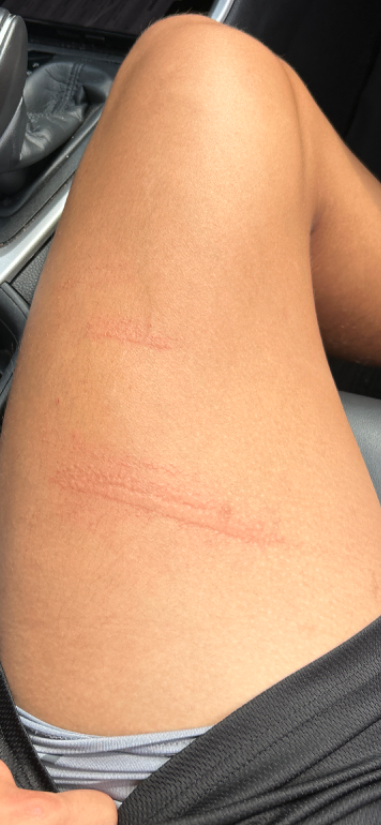Clinical context:
The patient indicates the condition has been present for about one day. This image was taken at a distance. The affected area is the leg.
Assessment:
The reviewing dermatologist's impression was: in keeping with Allergic Contact Dermatitis.